A dermatoscopic image of a skin lesion. A female subject 60 years old: 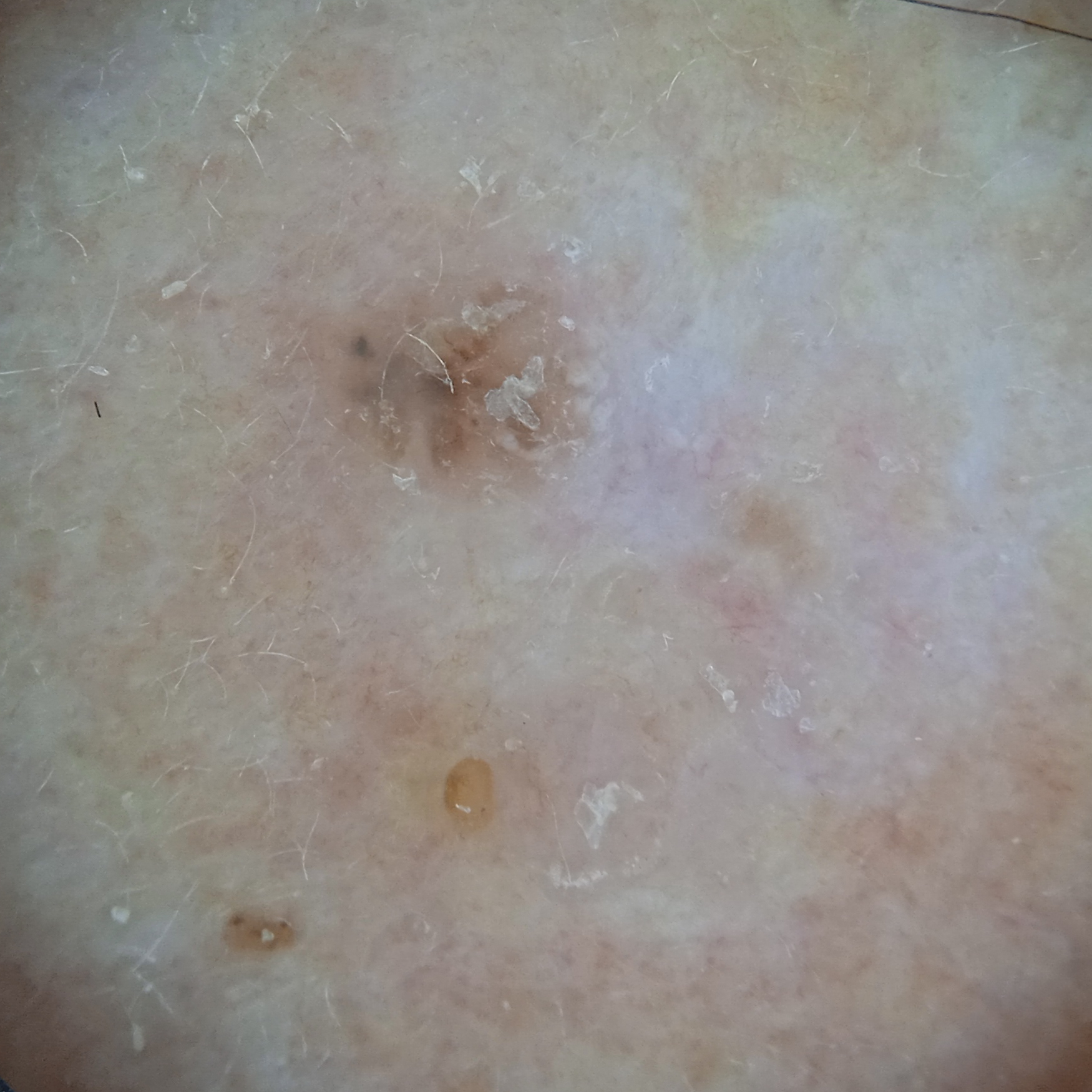The lesion is located on the face. The lesion is about 6.6 mm across. Histopathologically confirmed as a basal cell carcinoma, following excision, with a measured thickness of 1 mm.